A dermoscopic close-up of a skin lesion, a female subject aged 73 to 77:
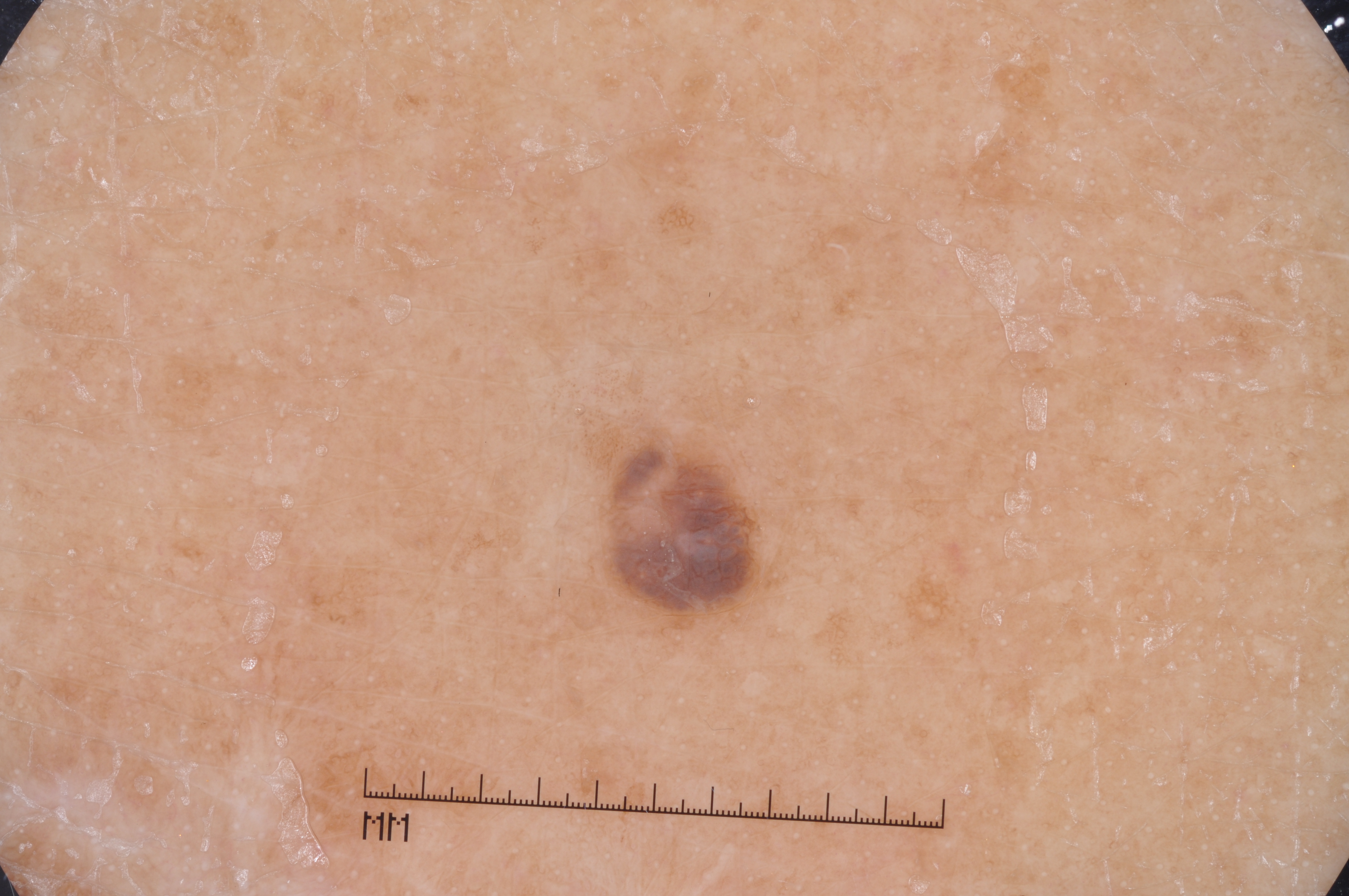Summary:
Dermoscopically, the lesion shows milia-like cysts. In (x1, y1, x2, y2) order, lesion location: [584,413,781,638]. The lesion takes up about 2% of the image.
Assessment:
Clinically diagnosed as a melanocytic nevus, a benign lesion.